The photograph is a close-up of the affected area:
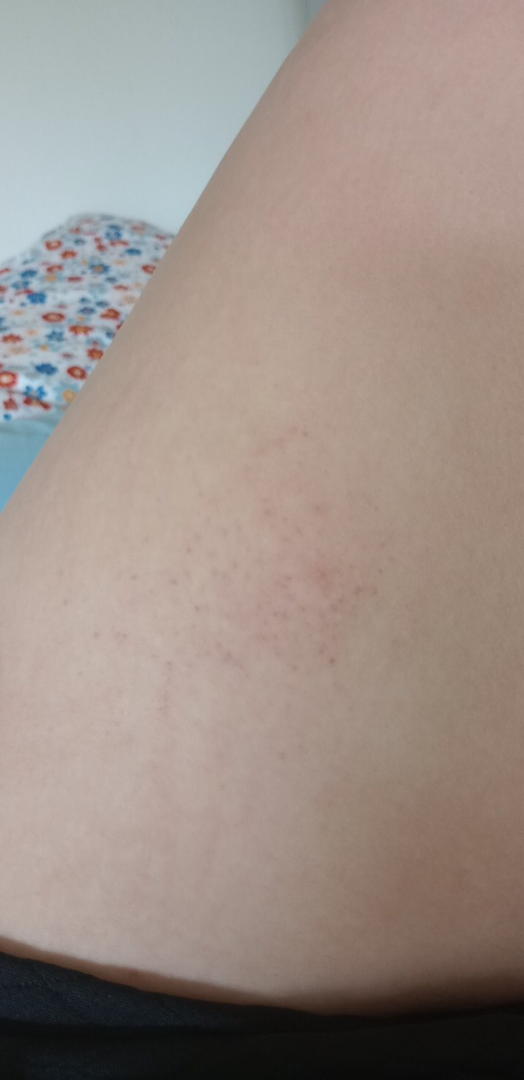Q: Could the case be diagnosed?
A: ungradable on photographic review